A dermoscopic close-up of a skin lesion: 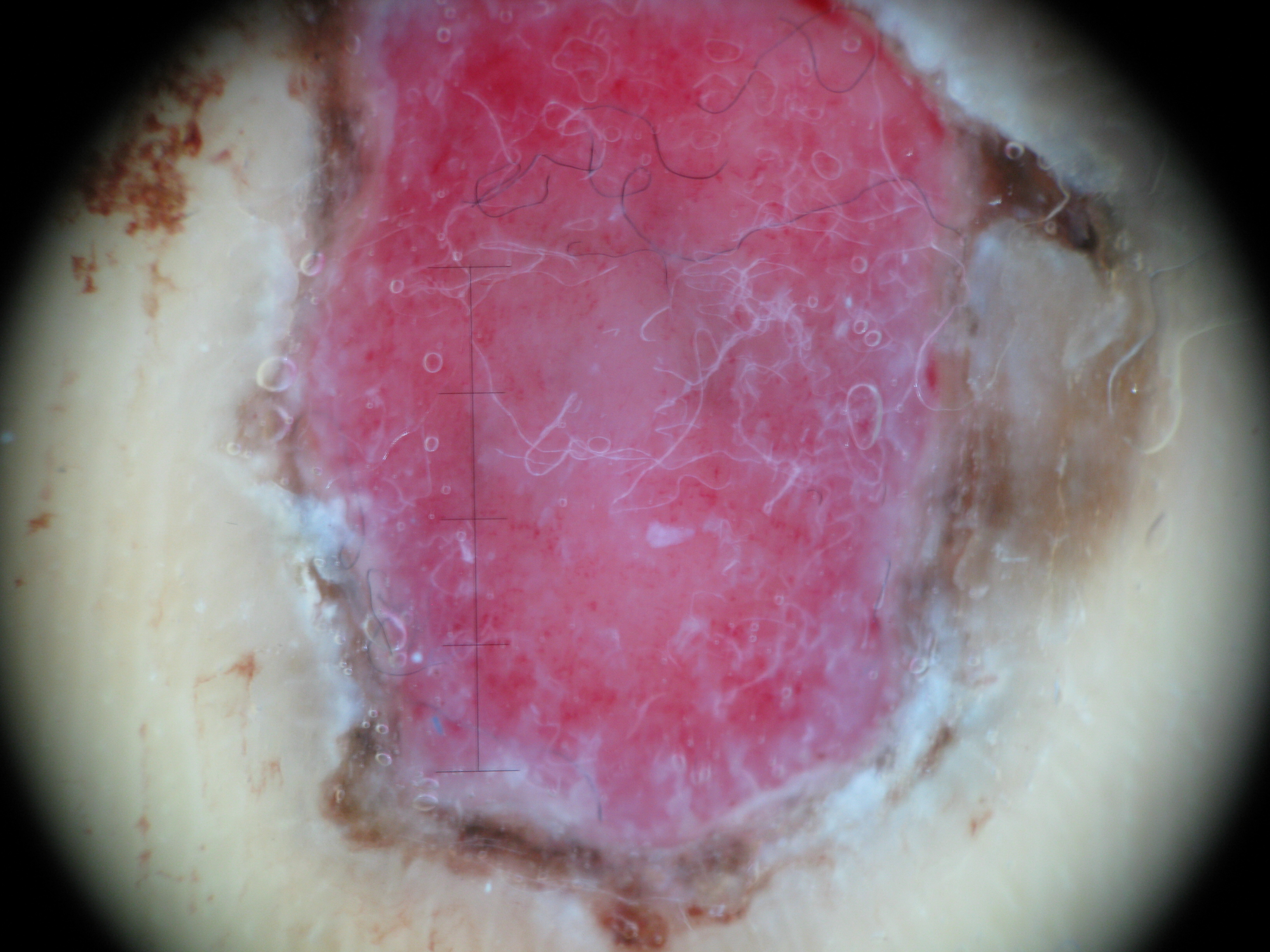Biopsy-confirmed as a malignant lesion — an acral nodular melanoma.